A dermatoscopic image of a skin lesion:
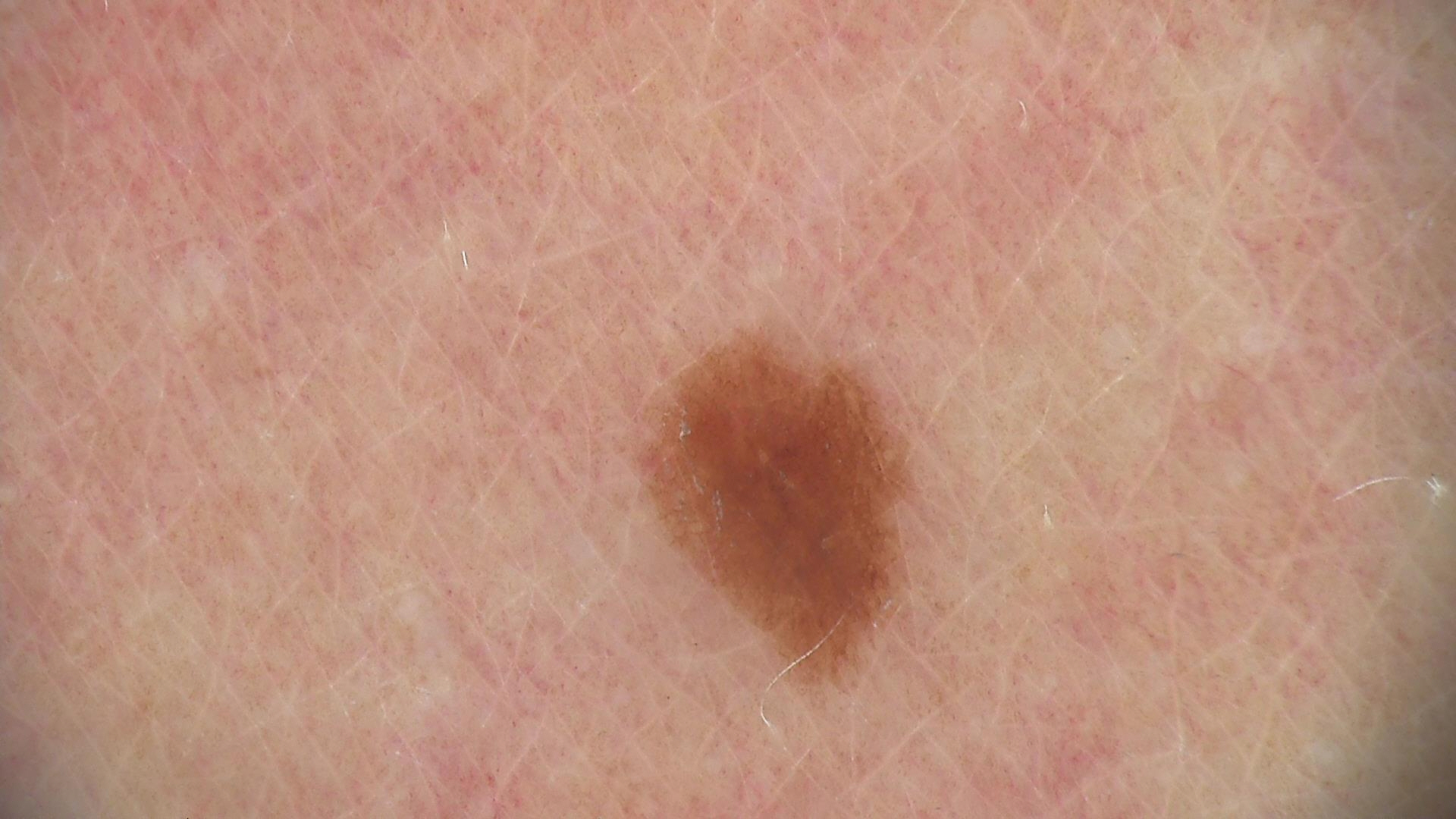Diagnosed as a dysplastic junctional nevus.